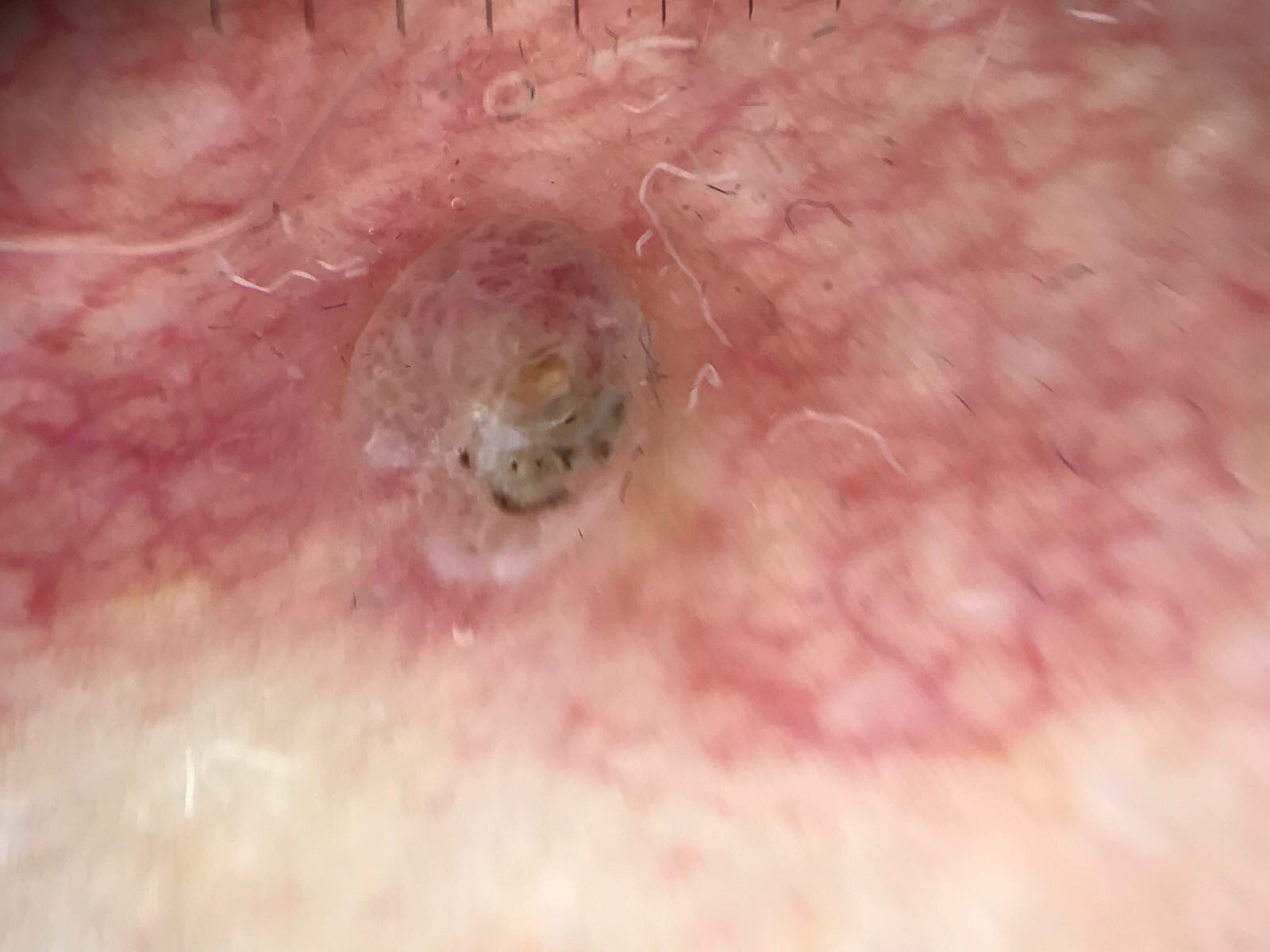Findings:
– modality: dermoscopy
– lesion type: keratinocytic
– class: squamous cell carcinoma (biopsy-proven)